The photograph is a close-up of the affected area.
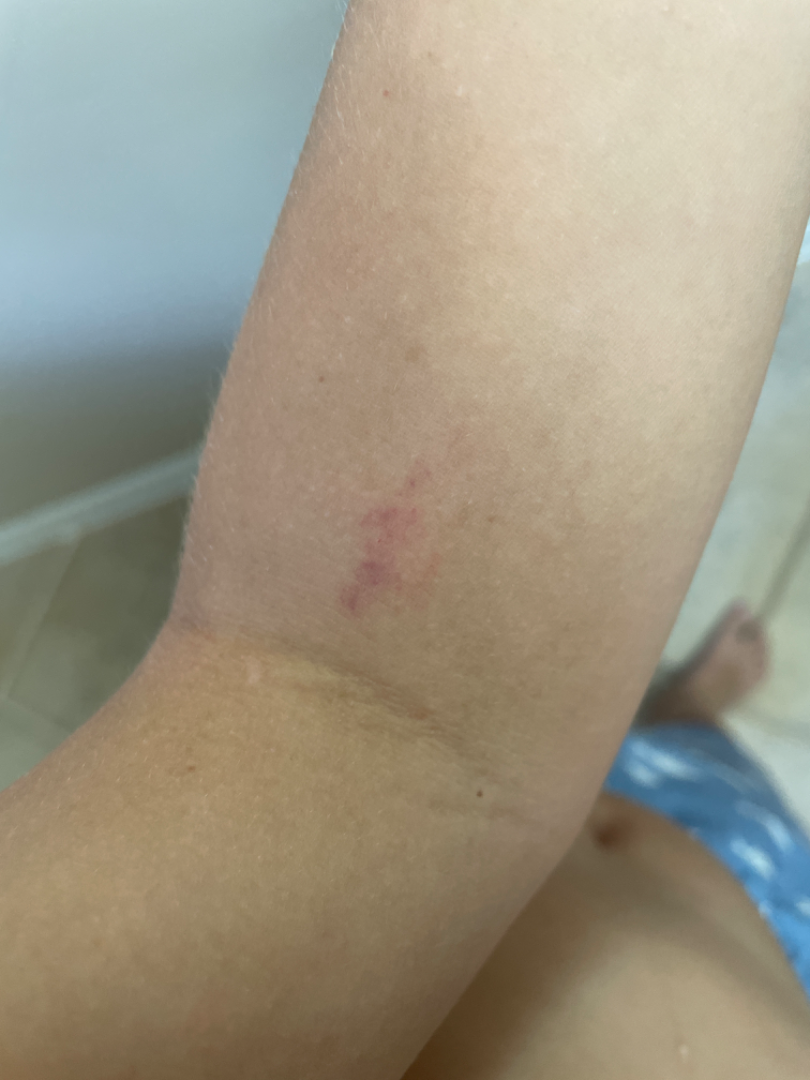No differential diagnosis could be assigned on photographic review.